A dermoscopic close-up of a skin lesion:
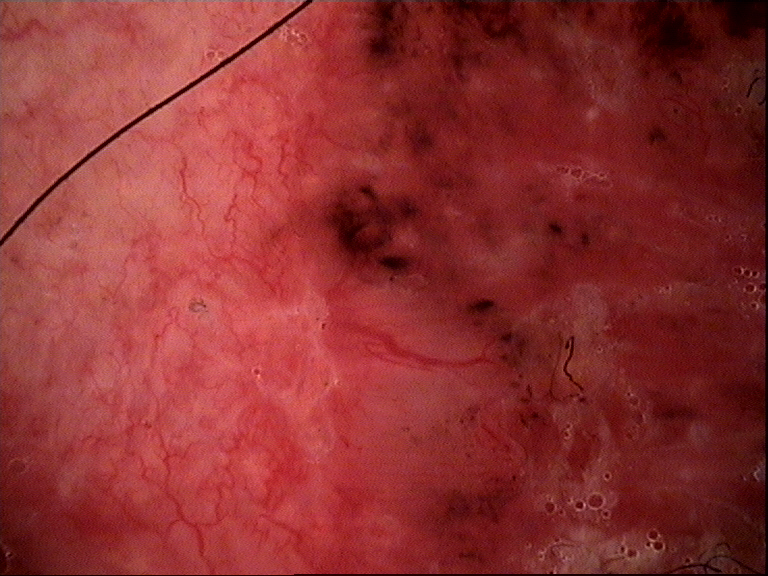The architecture is that of a keratinocytic lesion. Histopathology confirmed a basal cell carcinoma.